A dermoscopic photograph of a skin lesion:
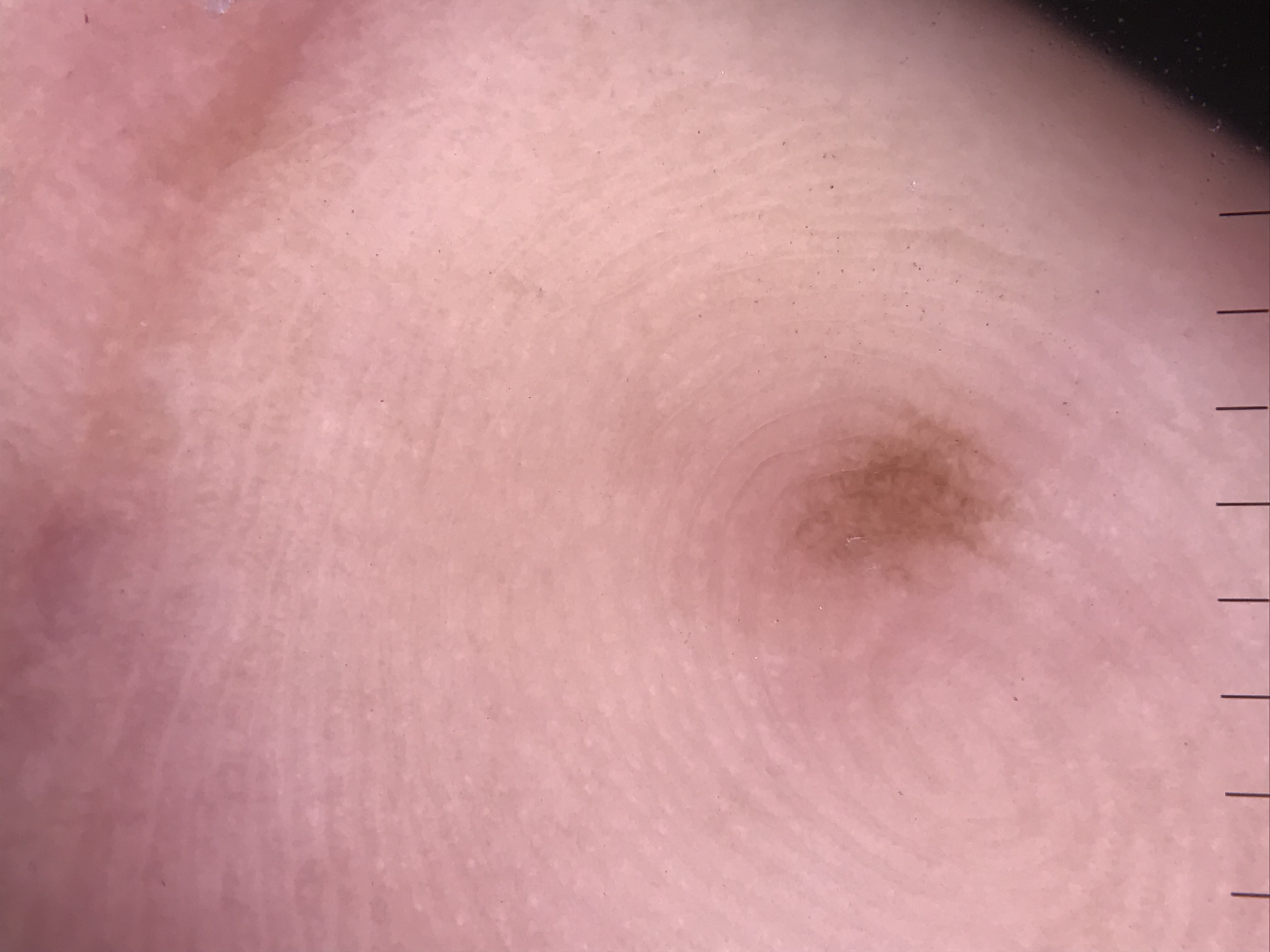The diagnosis was an acral junctional nevus.